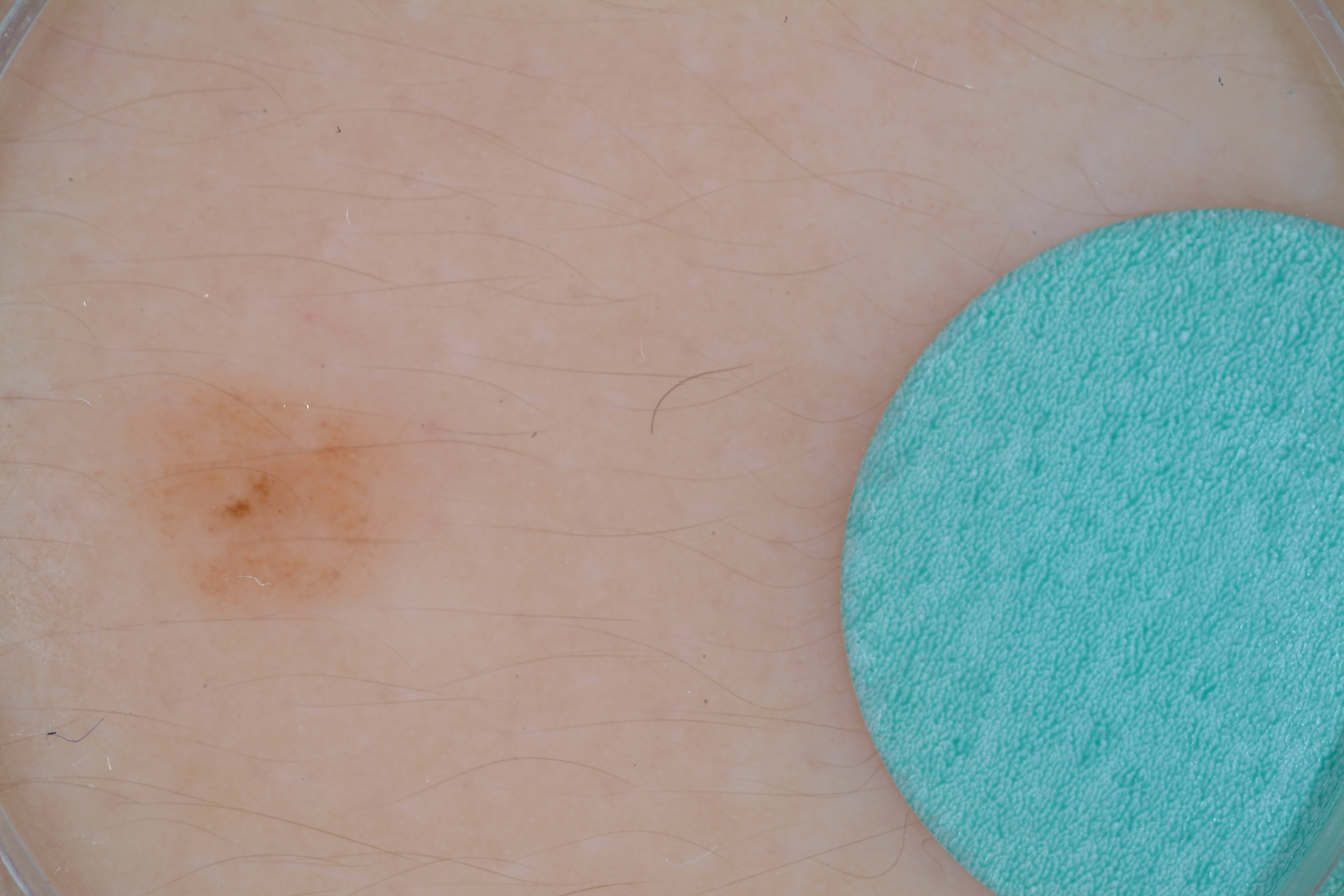Image and clinical context:
The patient is a female aged 8 to 12. A dermoscopic view of a skin lesion. As (left, top, right, bottom), the lesion spans [84,365,424,631]. On dermoscopy, the lesion shows no globules, milia-like cysts, streaks, pigment network, or negative network. A small lesion occupying a minor part of the field.
Assessment:
Expert review diagnosed this as a melanocytic nevus.